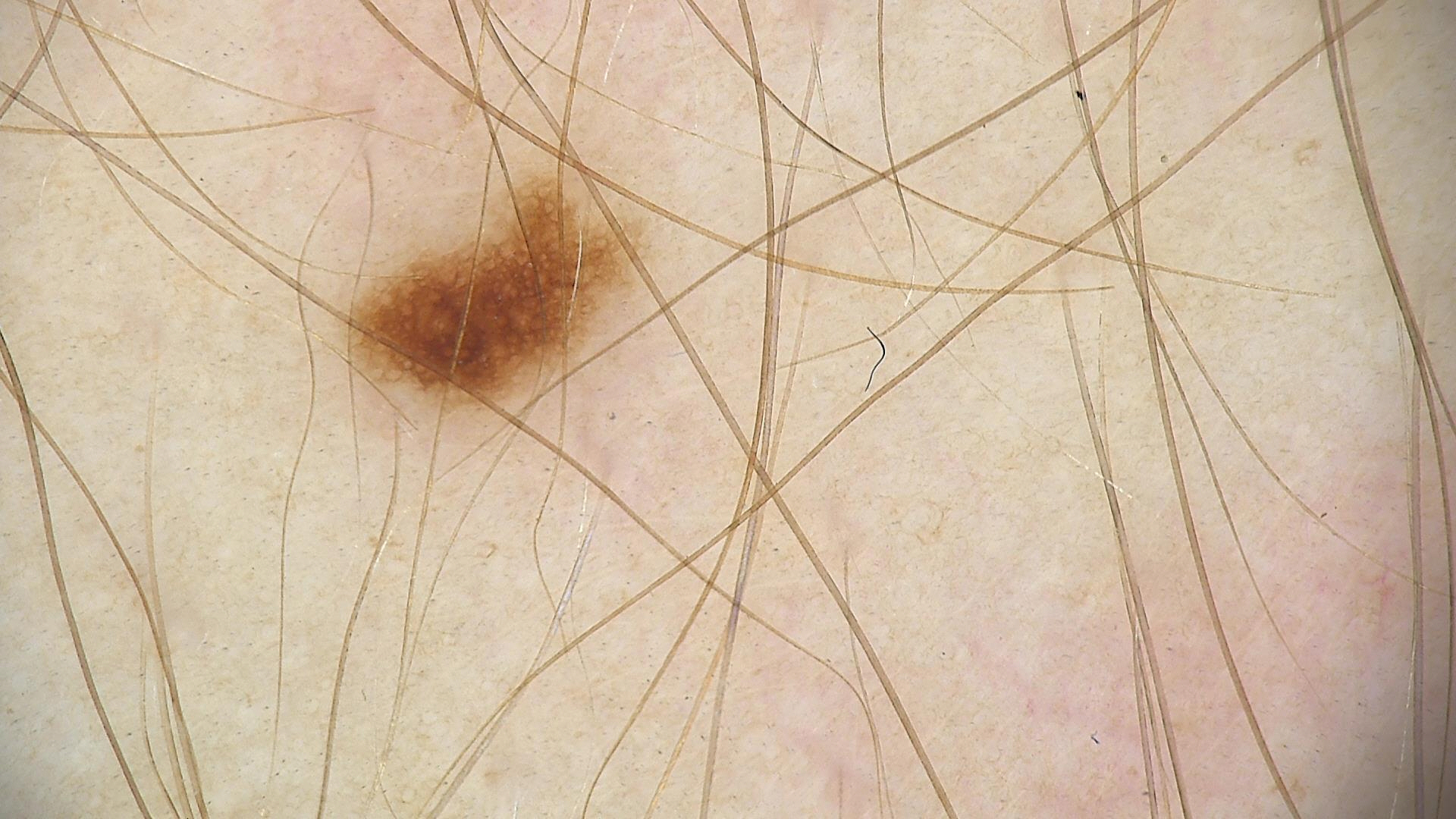A dermoscopic photograph of a skin lesion. Classified as a benign lesion — a dysplastic junctional nevus.